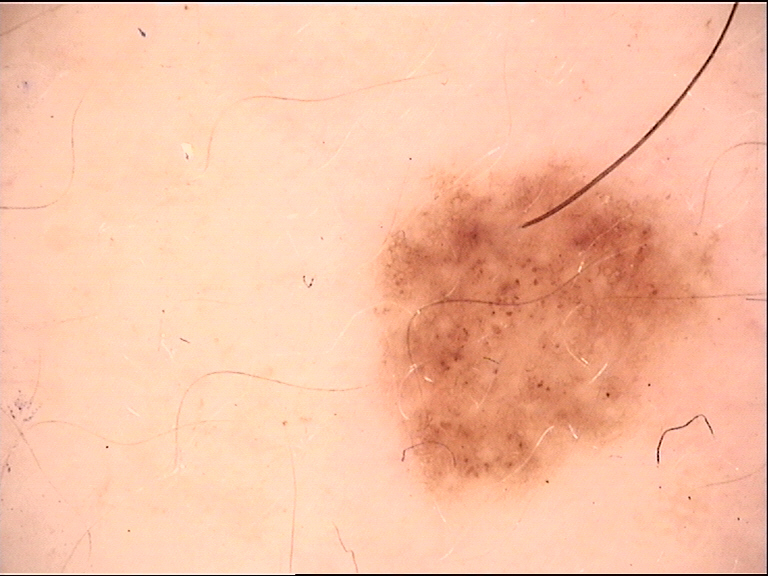diagnosis:
  name: dysplastic junctional nevus
  code: jd
  malignancy: benign
  super_class: melanocytic
  confirmation: expert consensus